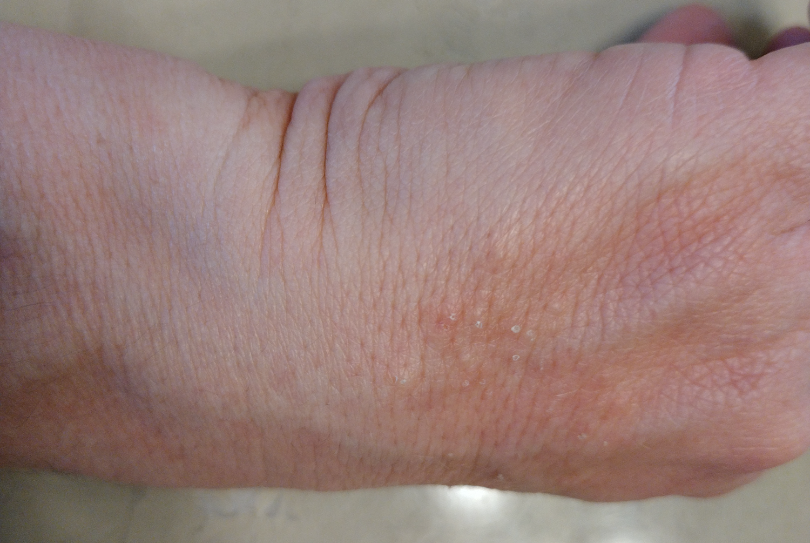differential:
  - Psoriasis
  - Eczema